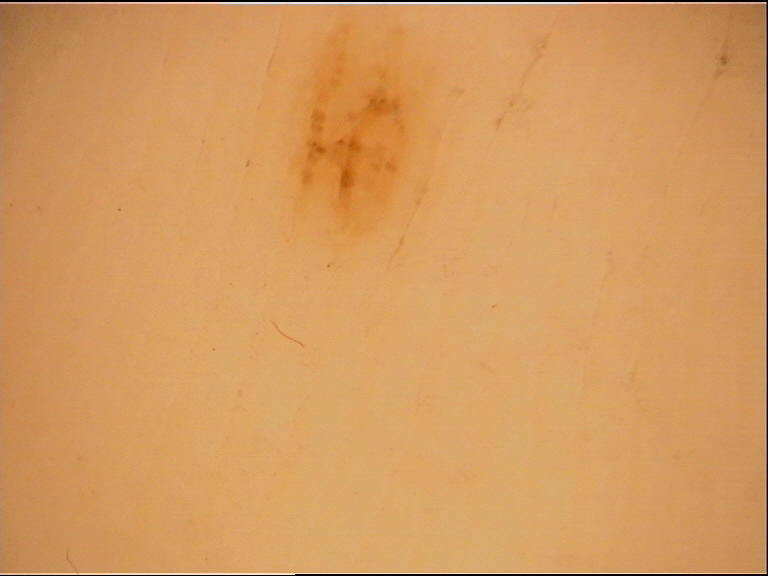Labeled as an acral junctional nevus.